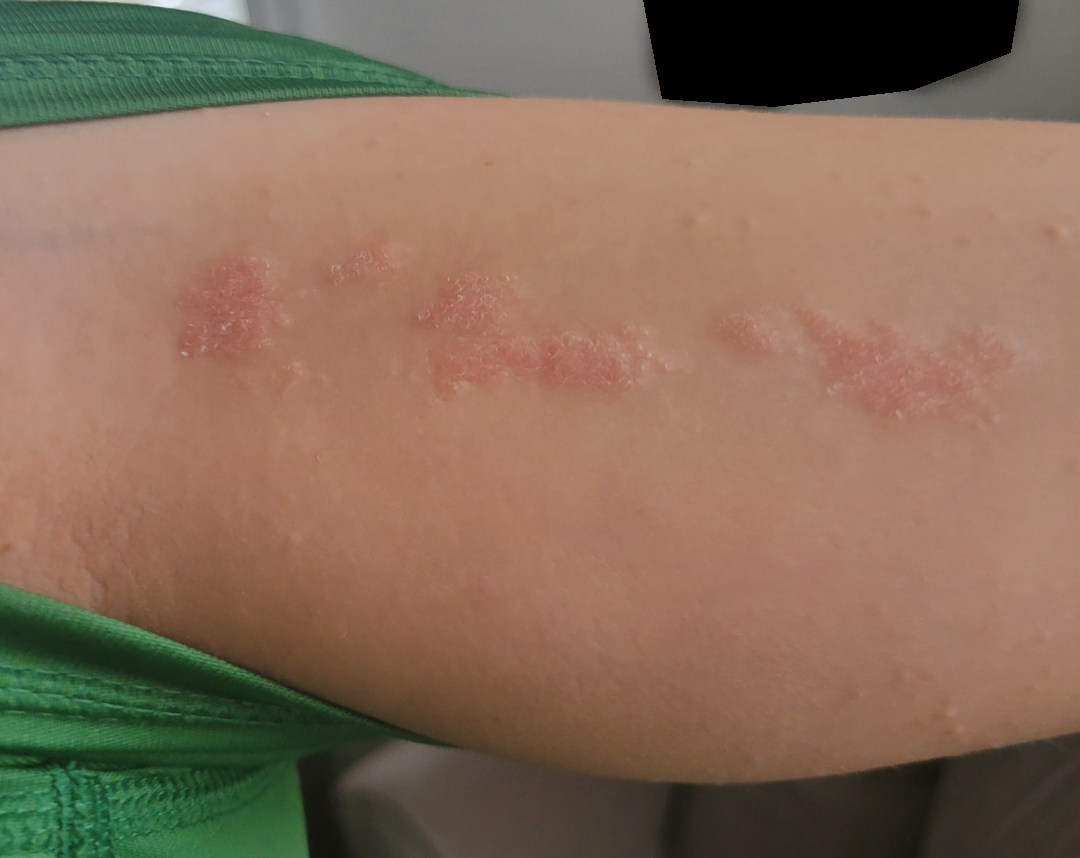<report>
<assessment>indeterminate from the photograph</assessment>
</report>